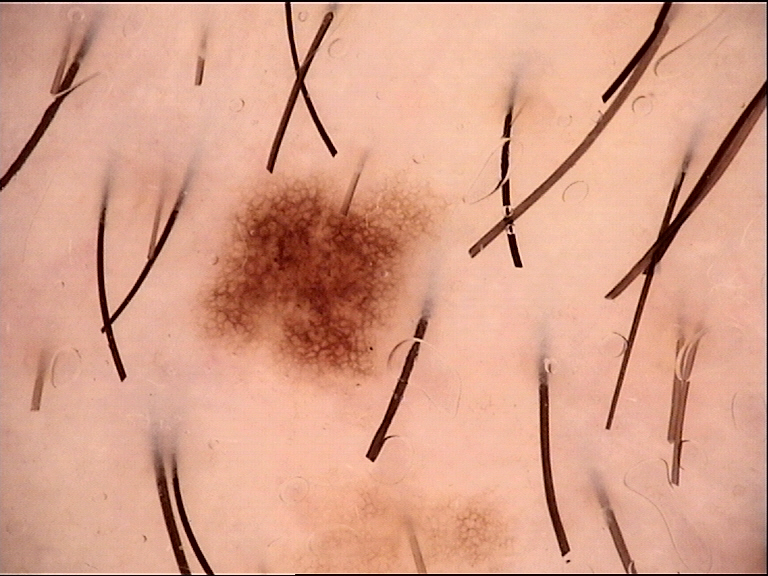Case: Dermoscopy of a skin lesion. Conclusion: Labeled as a dysplastic junctional nevus.